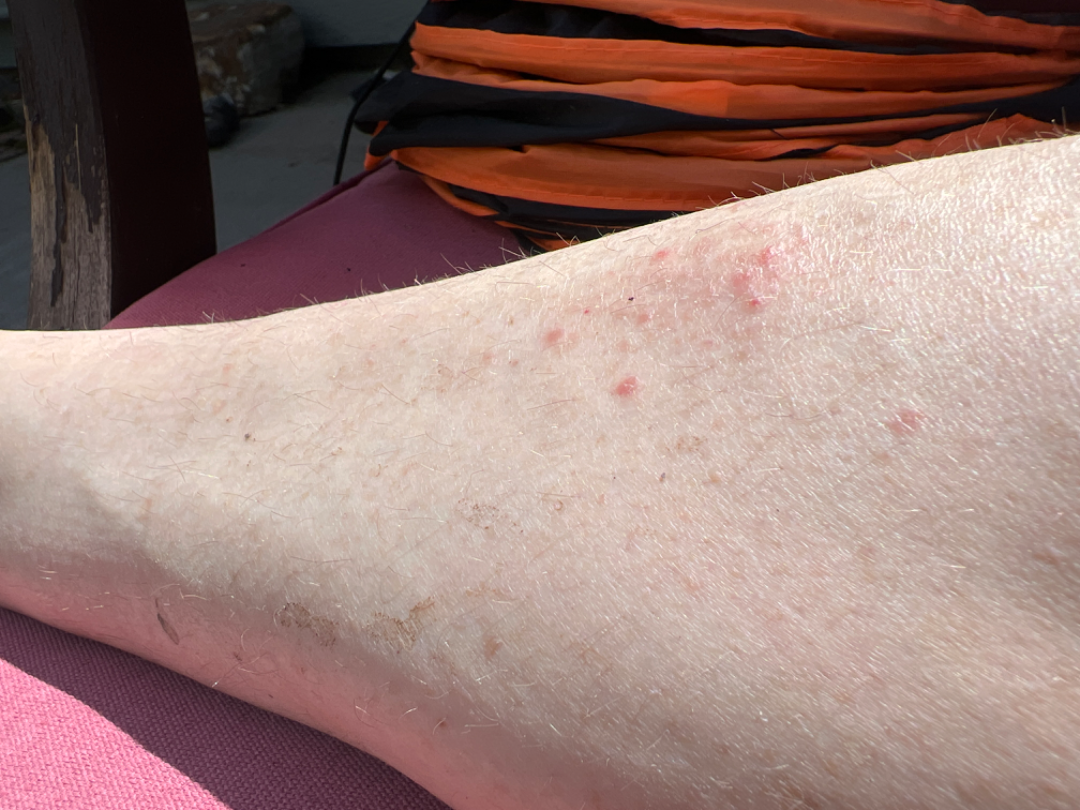Findings: Reviewed remotely by one dermatologist: Eczema and Stasis Dermatitis were considered with similar weight; less probable is Folliculitis.